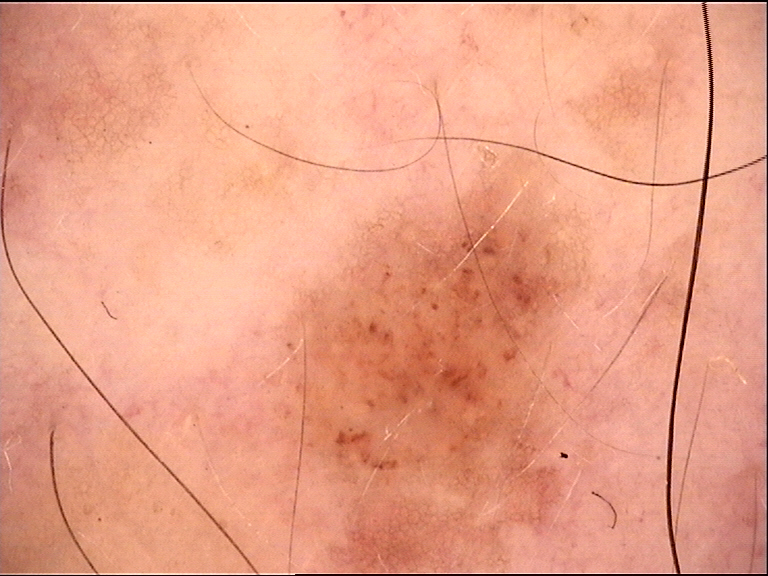diagnostic label = dysplastic junctional nevus (expert consensus).